A dermatoscopic image of a skin lesion.
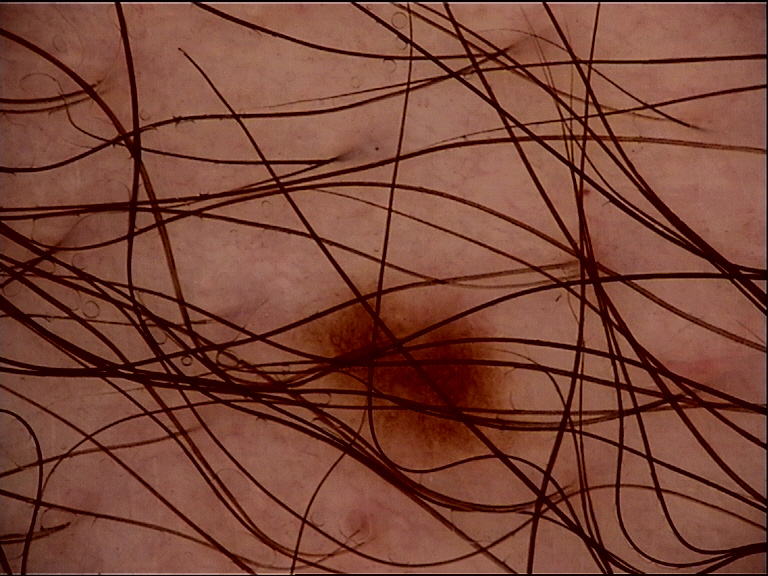The architecture is that of a banal lesion.
The diagnosis was a junctional nevus.